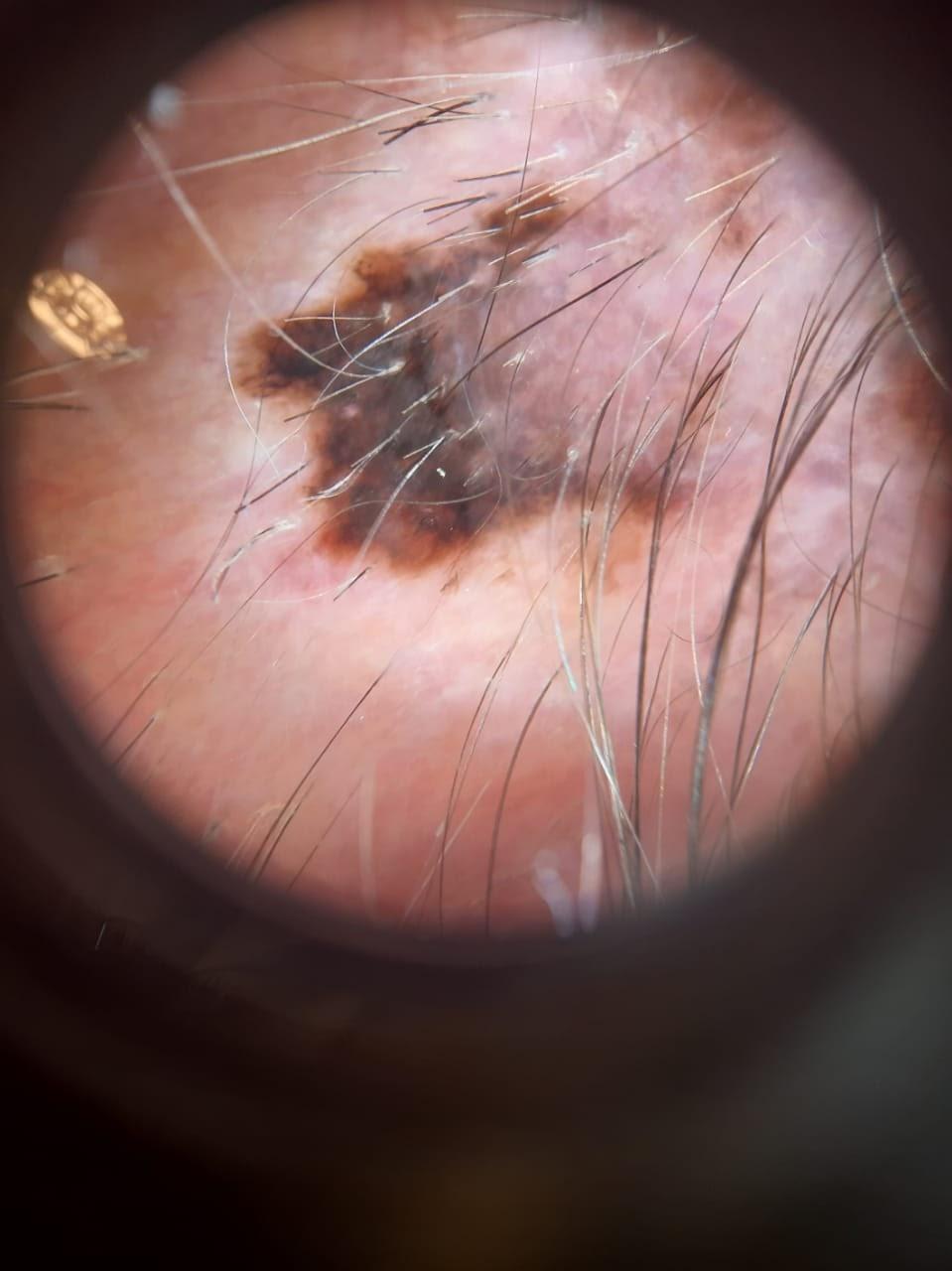A female subject aged approximately 85 or older.
A dermoscopic image of a skin lesion.
The patient is FST II.
The biopsy diagnosis was a malignancy — a melanoma.